Fitzpatrick skin type V; a close-up photograph; the lesion is described as raised or bumpy; no constitutional symptoms were reported; the arm is involved; symptoms reported: burning; present for about one day — 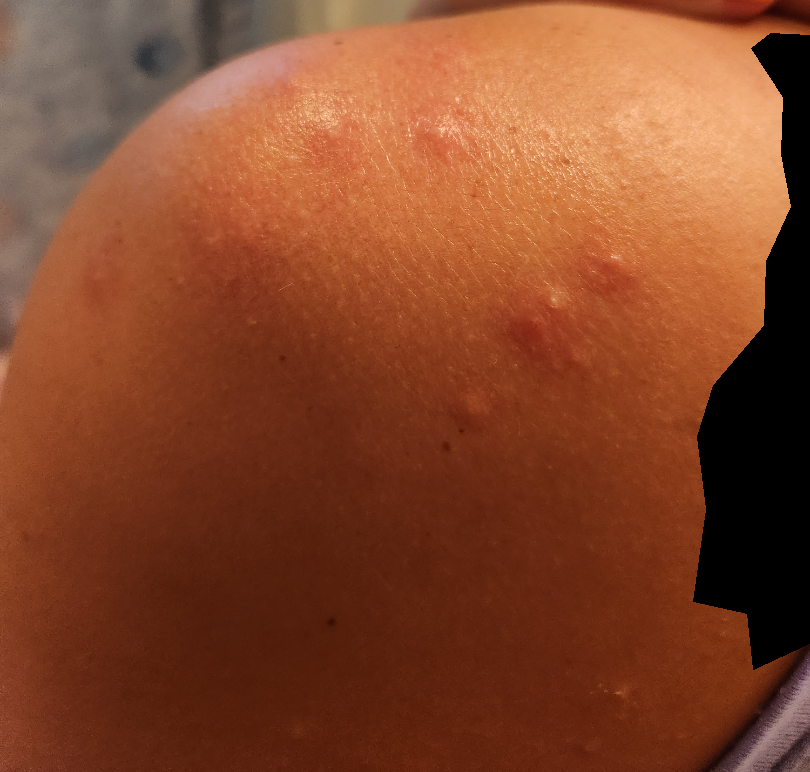Findings:
The case was indeterminate on photographic review.